A skin lesion imaged with a dermatoscope.
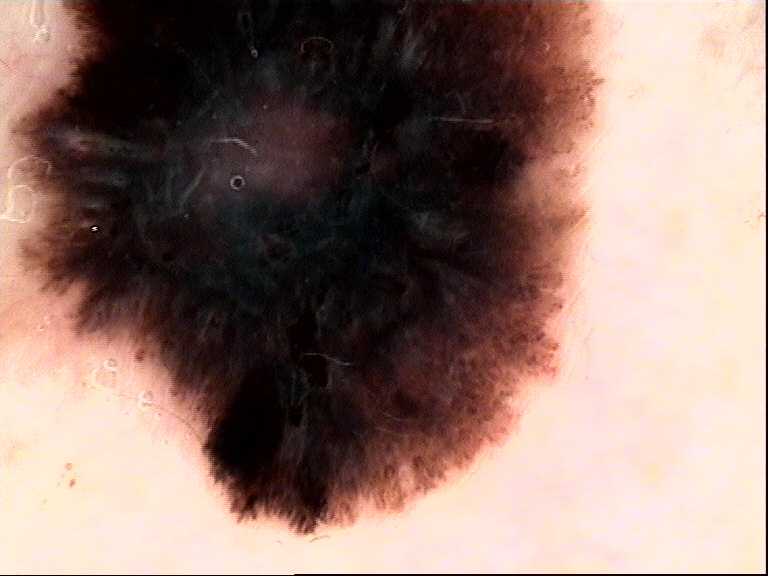The biopsy diagnosis was a malignancy — a melanoma.